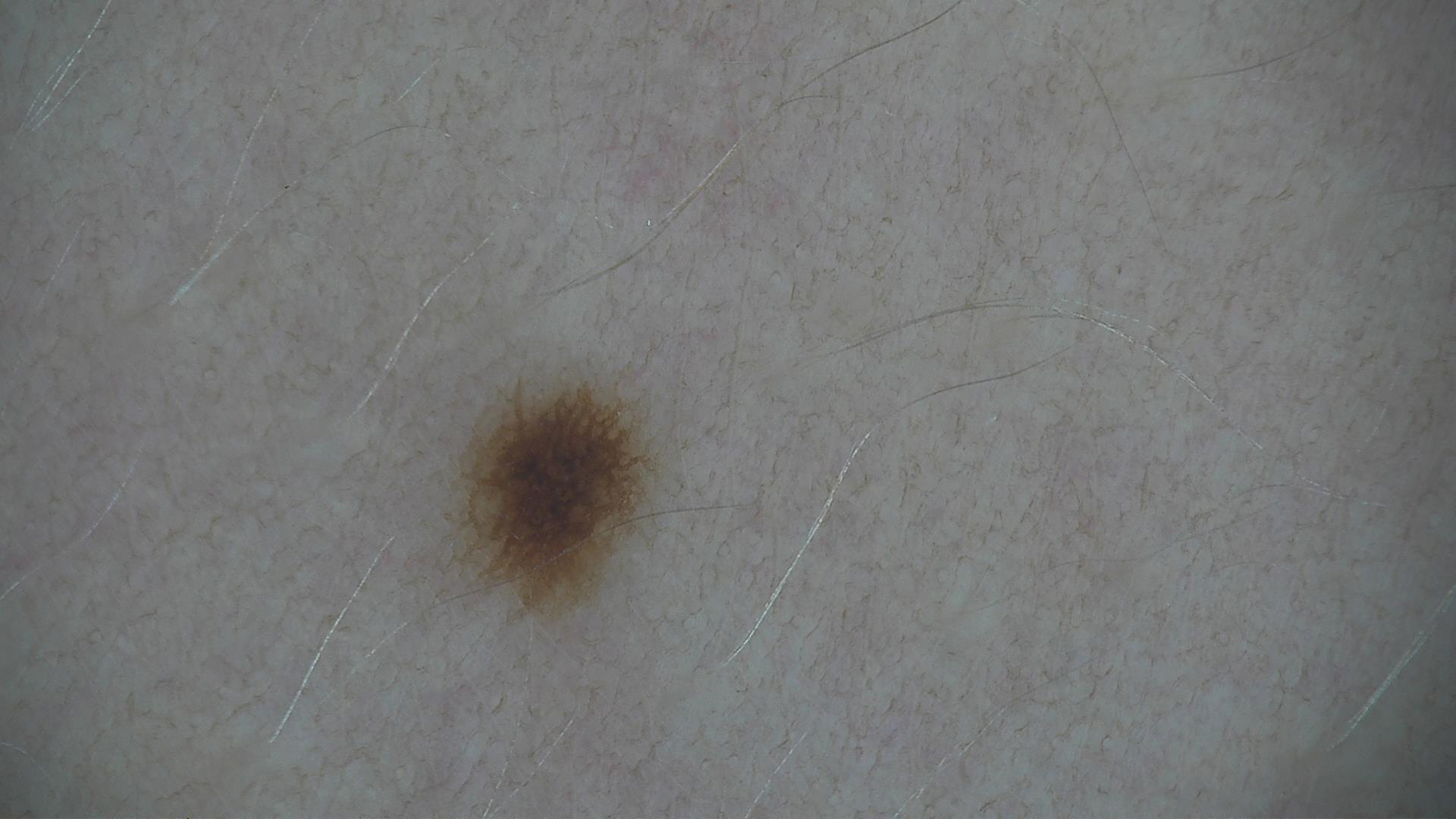A skin lesion imaged with a dermatoscope.
Diagnosed as a dysplastic junctional nevus.